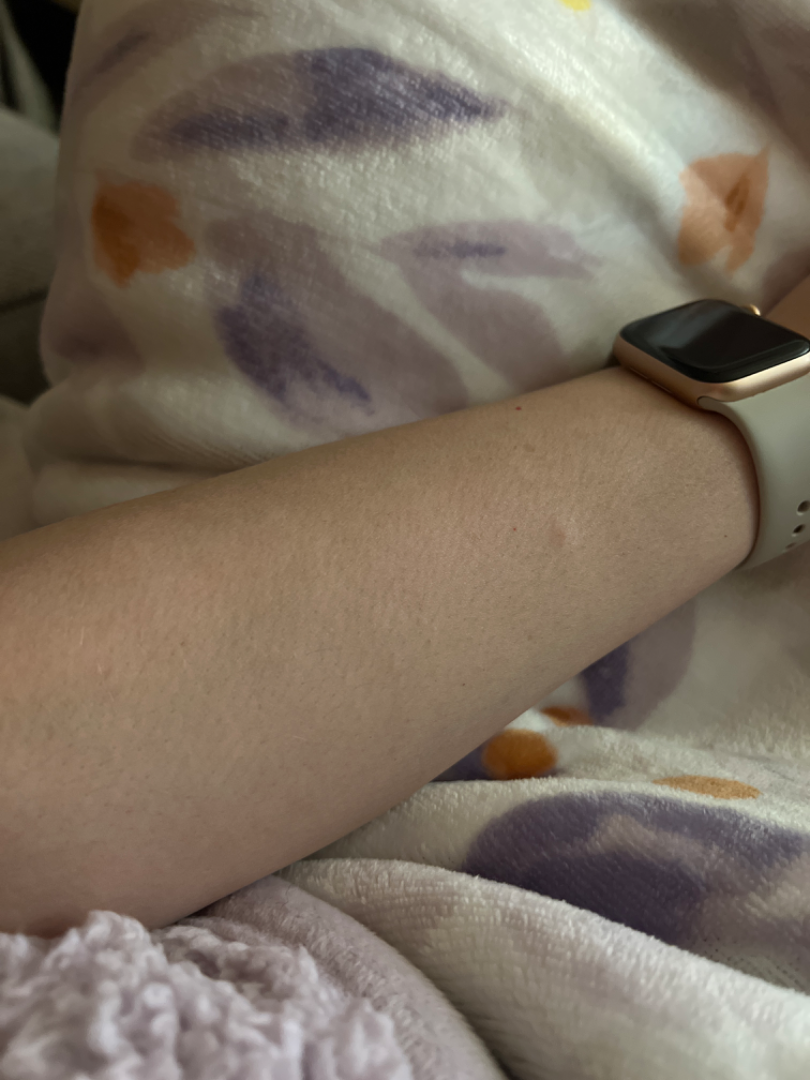| feature | finding |
|---|---|
| texture | raised or bumpy |
| patient's own categorization | a rash |
| photo taken | at a distance |
| body site | arm and leg |